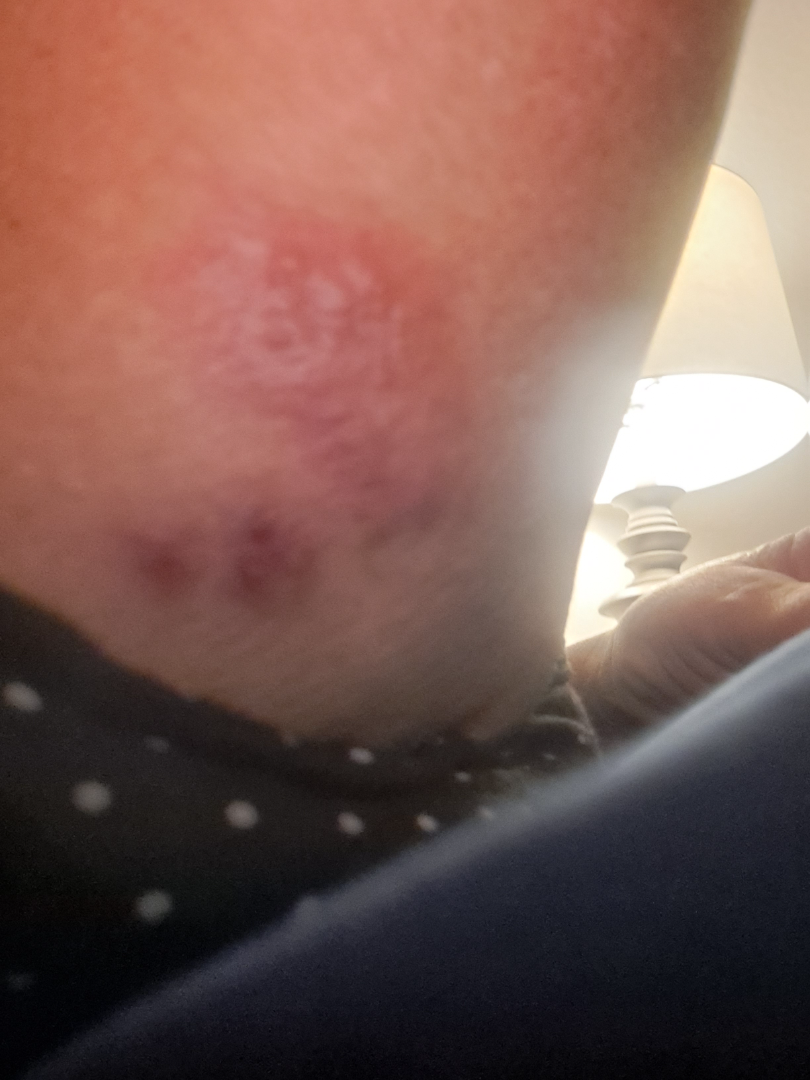<dermatology_case>
<assessment>indeterminate</assessment>
<shot_type>at an angle</shot_type>
</dermatology_case>